A male patient in their late 50s. Recorded as FST III. A clinical photo of a skin lesion taken with a smartphone: 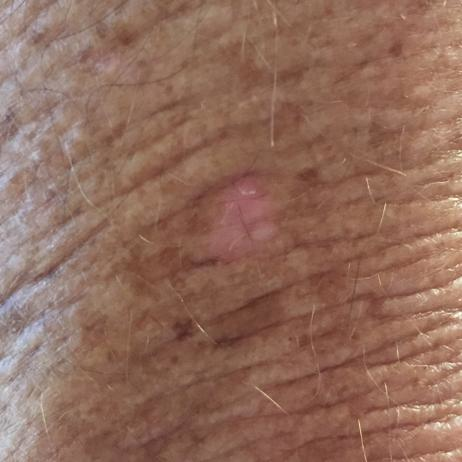The lesion was found on an arm.
The lesion is roughly 4 by 3 mm.
By the patient's account, the lesion itches, but is not elevated.
Expert review favored an actinic keratosis.